A female subject, in their mid- to late 30s · a dermoscopic image of a skin lesion — 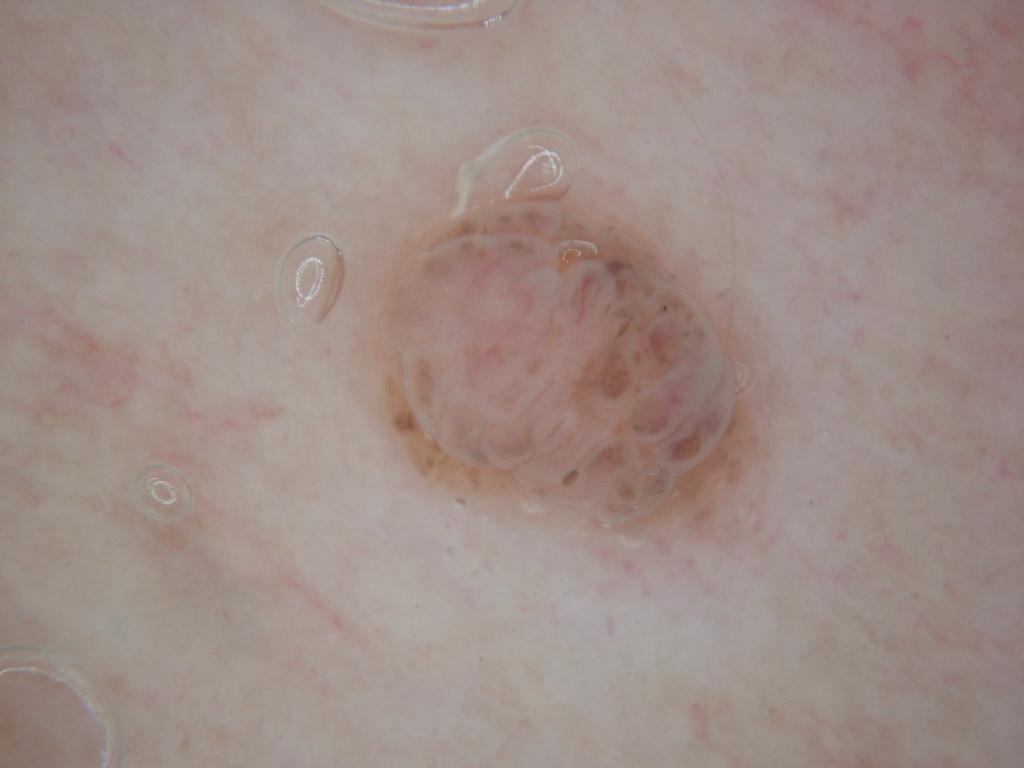Findings:
In (x1, y1, x2, y2) order, the lesion spans [379,193,780,544]. Dermoscopy demonstrates globules, with no milia-like cysts, pigment network, negative network, or streaks.
Impression:
Clinically diagnosed as a melanocytic nevus, a benign skin lesion.